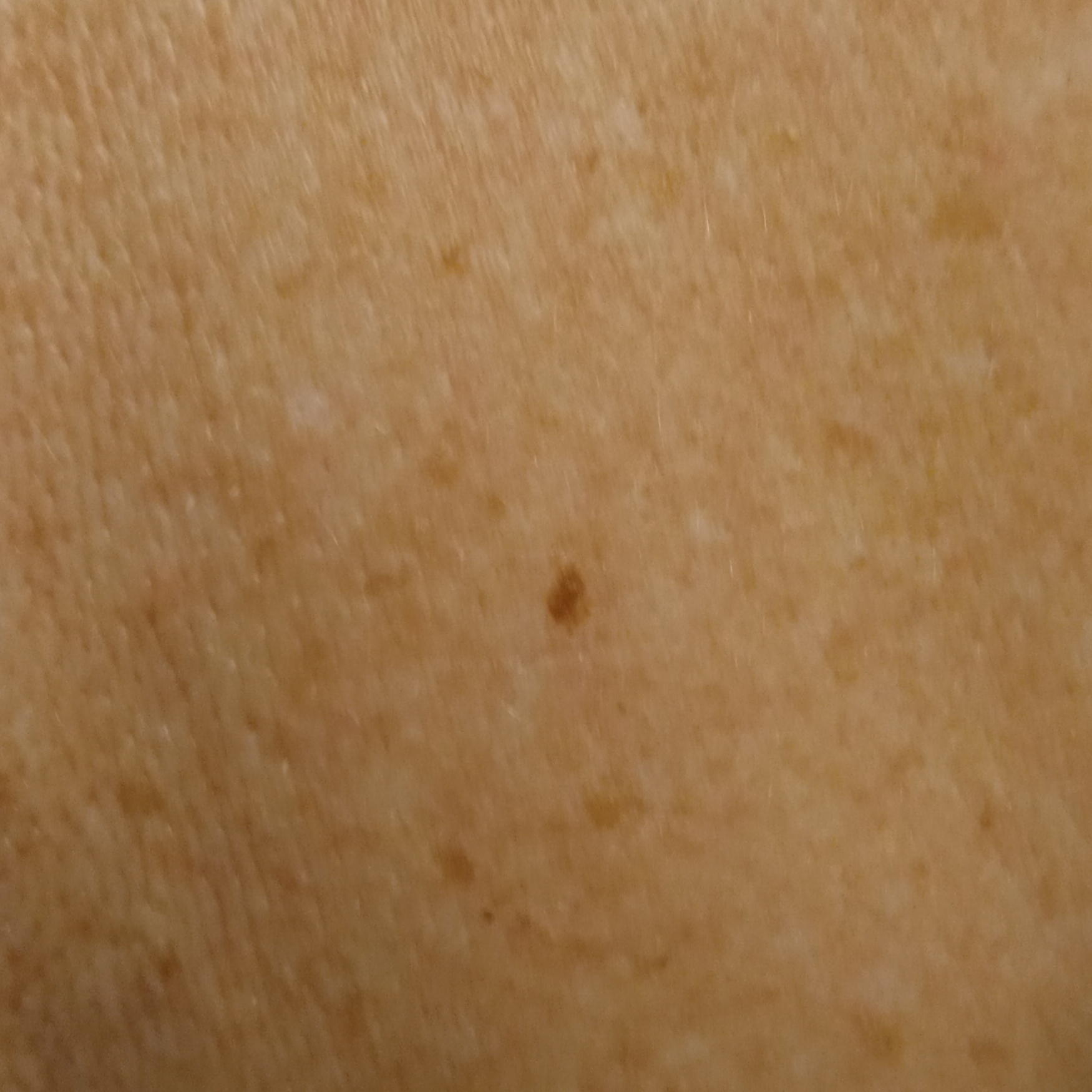Case summary:
The patient describes having few moles overall. The patient says their skin reddens with sun exposure. A female patient aged 73. The lesion involves the back. Measuring roughly 3.9 mm.
Conclusion:
Dermatologist review favored a seborrheic keratosis.